A dermatoscopic image of a skin lesion: 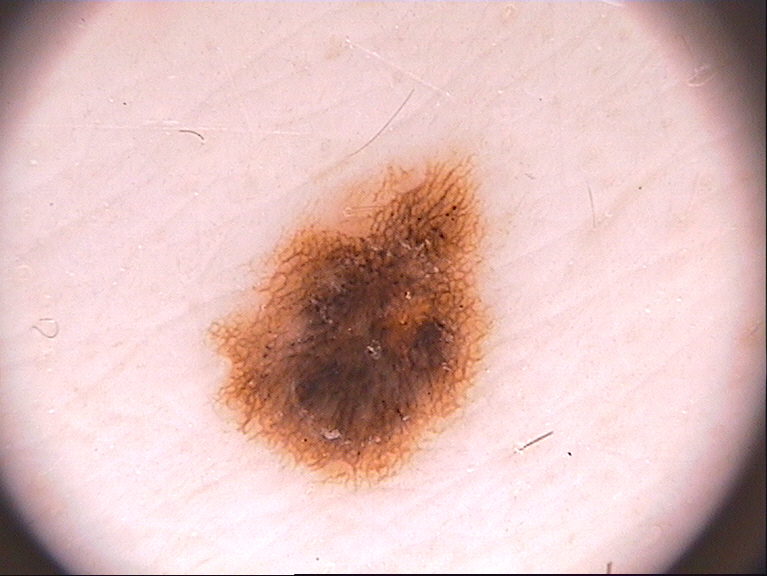{"lesion_location": {"bbox_xyxy": [210, 147, 493, 483]}, "diagnosis": {"name": "melanocytic nevus", "malignancy": "benign", "lineage": "melanocytic", "provenance": "clinical"}}